The contributor reports the lesion is raised or bumpy; reported lesion symptoms include itching; the head or neck and arm are involved; this image was taken at an angle.
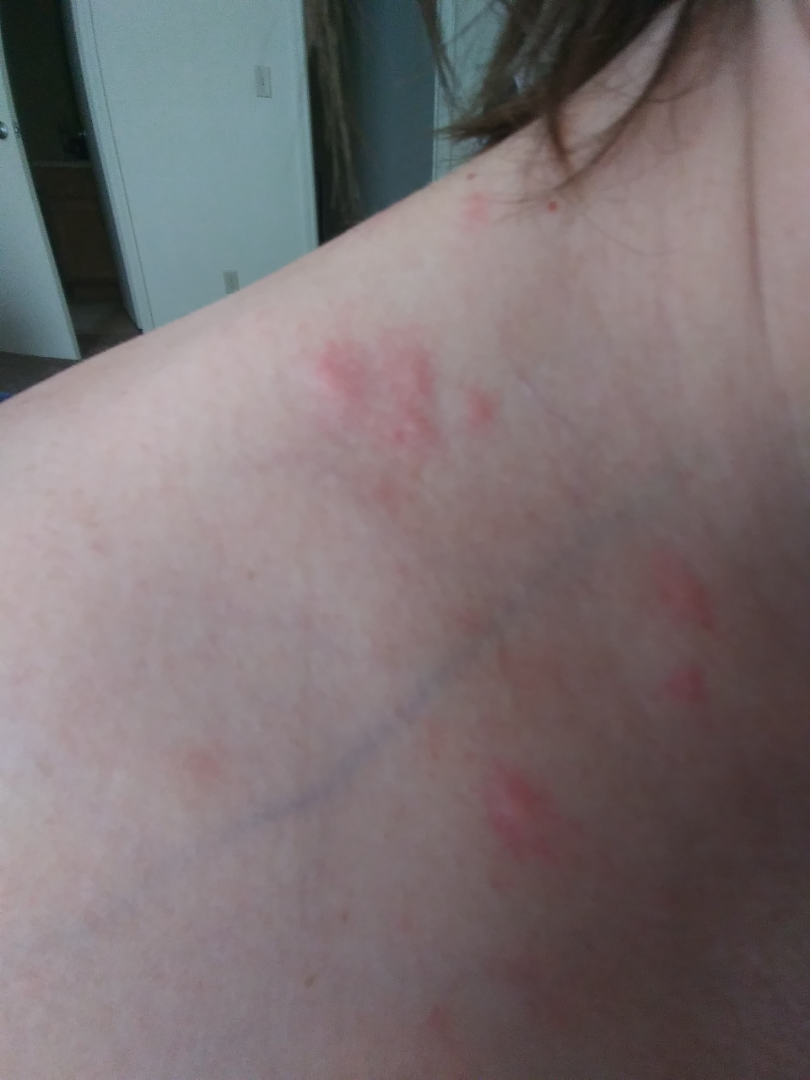Assessment:
A single dermatologist reviewed the case: the reviewer's impression was Insect Bite.